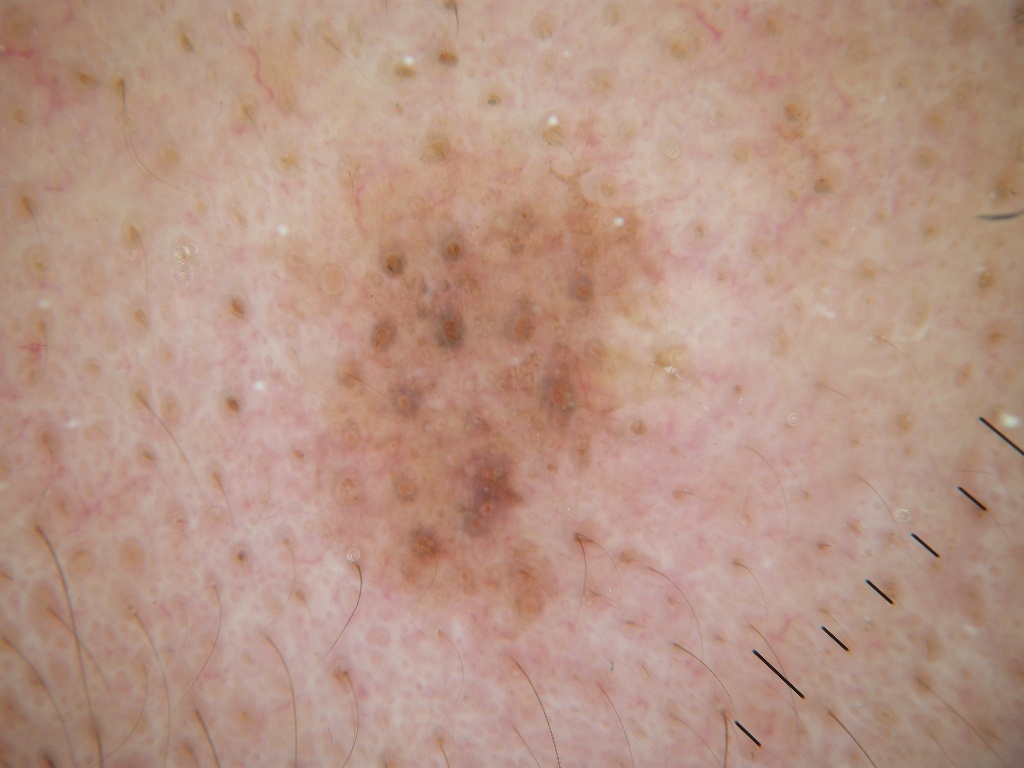Image and clinical context: The patient is a male approximately 60 years of age. A dermatoscopic image of a skin lesion. Dermoscopic assessment notes milia-like cysts. As (left, top, right, bottom), the lesion is located at box(279, 110, 709, 658). The lesion takes up a moderate portion of the field. Conclusion: Histopathological examination showed a melanoma.